A male patient aged 83; a smartphone photograph of a skin lesion:
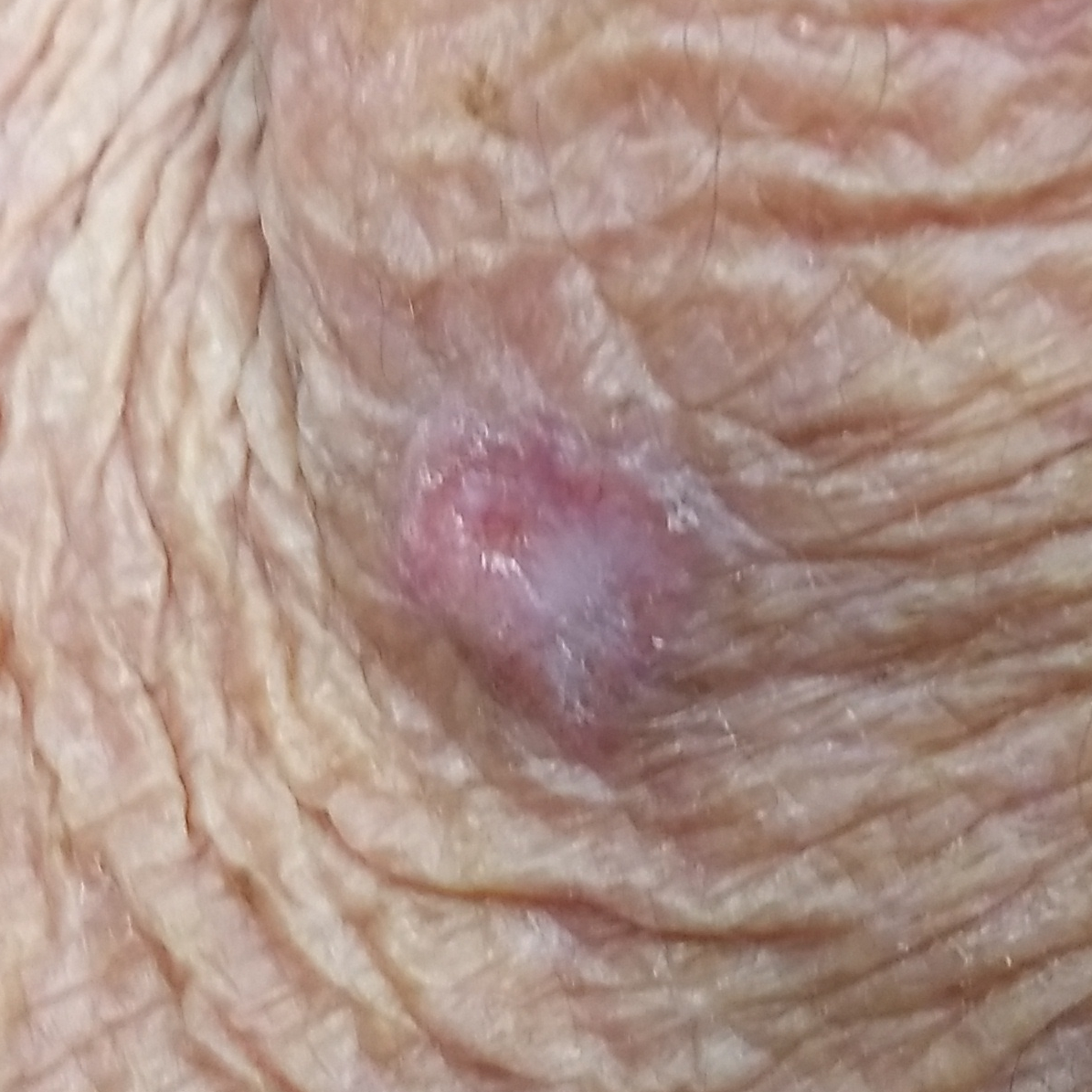anatomic site = a forearm; reported symptoms = growth, itching; diagnosis = basal cell carcinoma (biopsy-proven).